This is a dermoscopic photograph of a skin lesion:
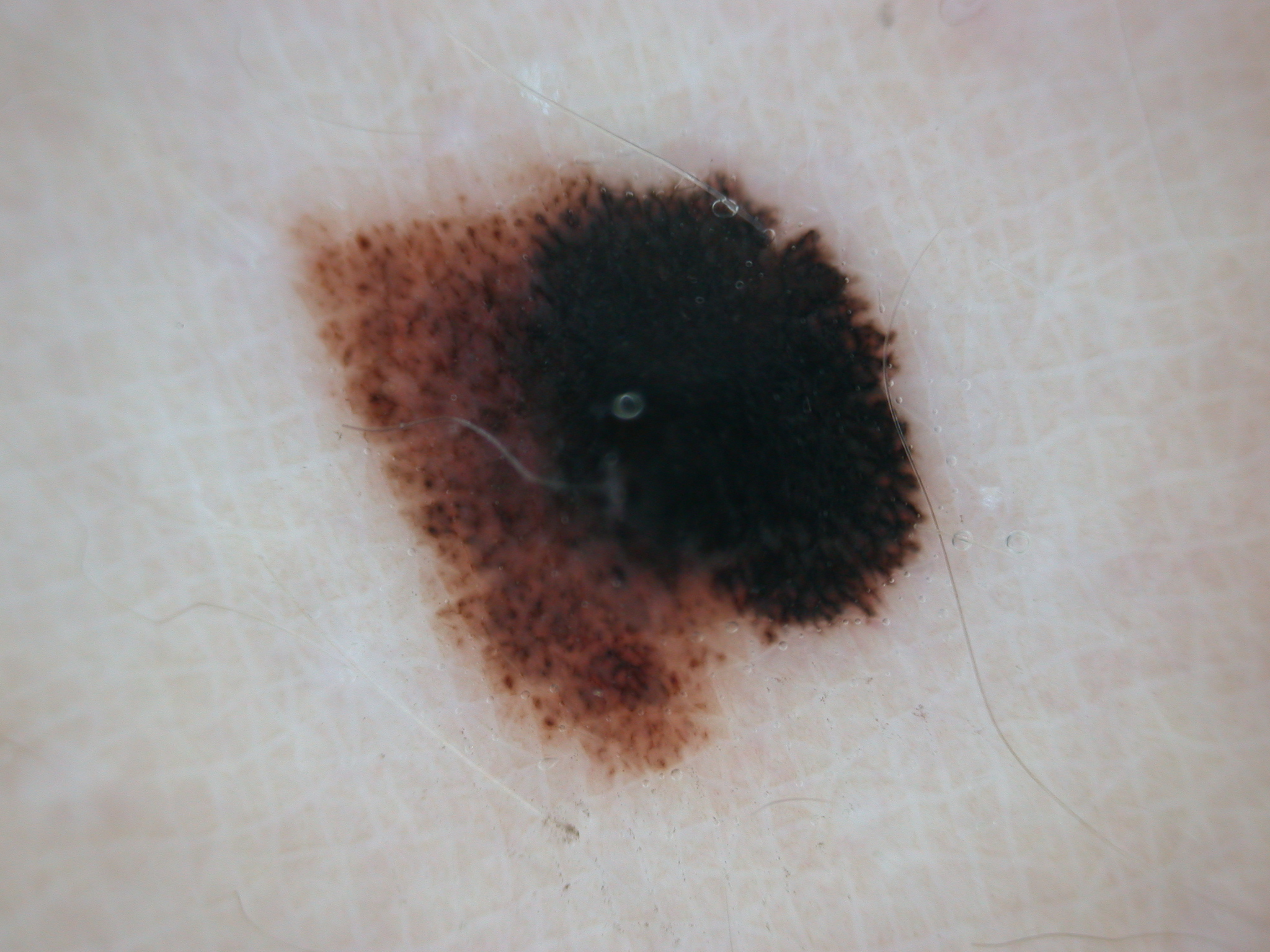Dermoscopic examination shows pigment network, globules, and streaks, with no negative network or milia-like cysts. As (left, top, right, bottom), lesion location: (283, 161, 928, 798). A moderately sized lesion. Expert review diagnosed this as a melanocytic nevus.